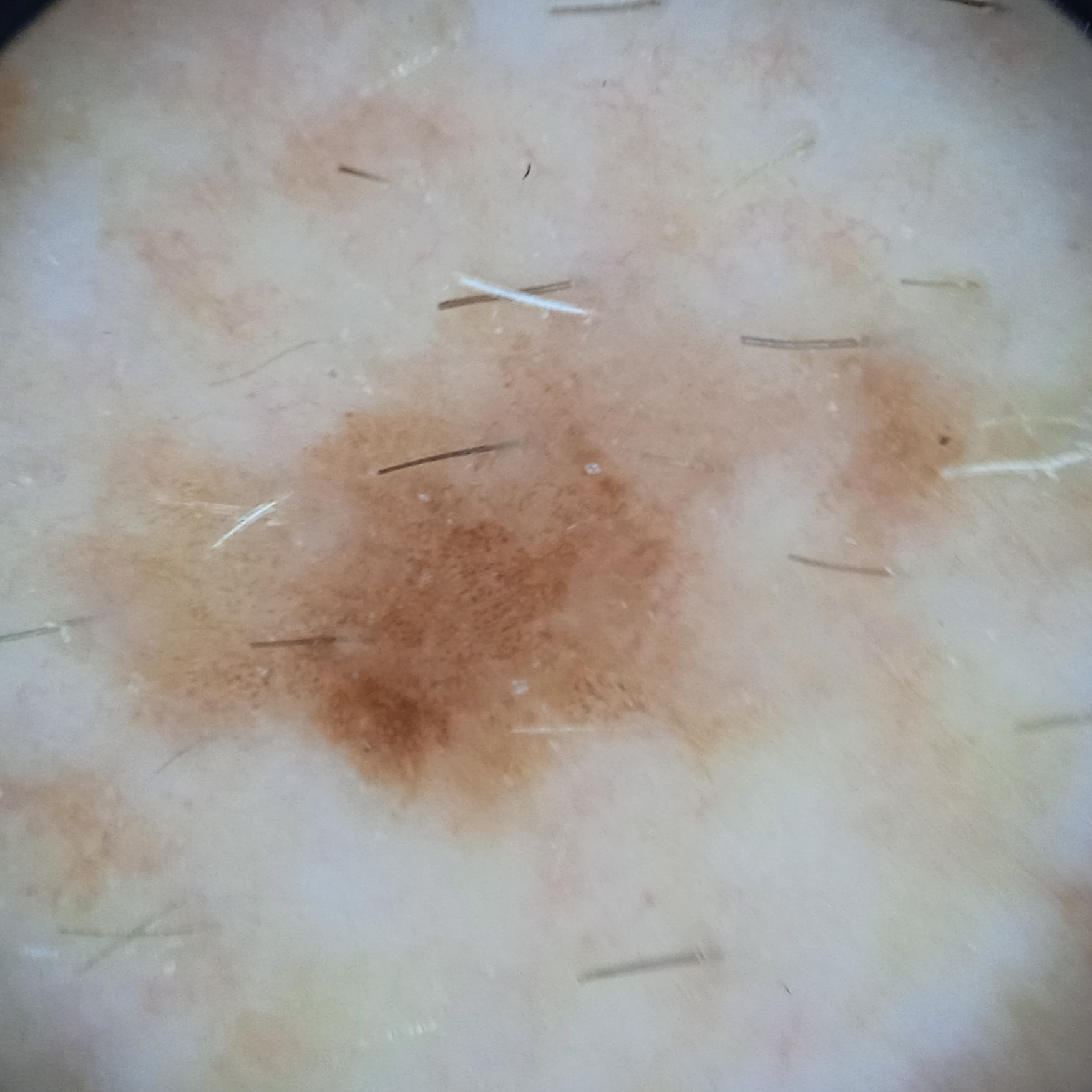<lesion>
  <image>dermatoscopic image</image>
  <lesion_location>the torso</lesion_location>
  <lesion_size>
    <diameter_mm>6.6</diameter_mm>
  </lesion_size>
  <diagnosis>
    <name>melanoma</name>
    <malignancy>malignant</malignancy>
  </diagnosis>
</lesion>